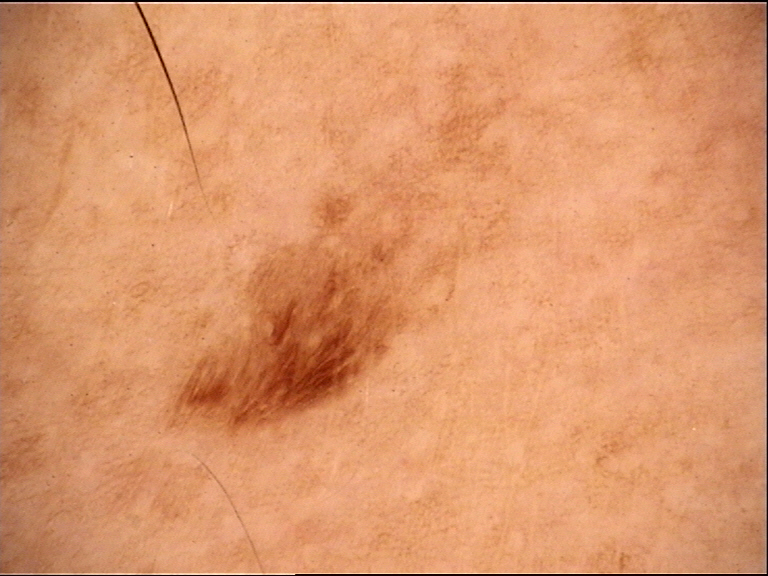A skin lesion imaged with a dermatoscope. The morphology is that of a keratinocytic lesion. Classified as a seborrheic keratosis.